A dermoscopic close-up of a skin lesion: 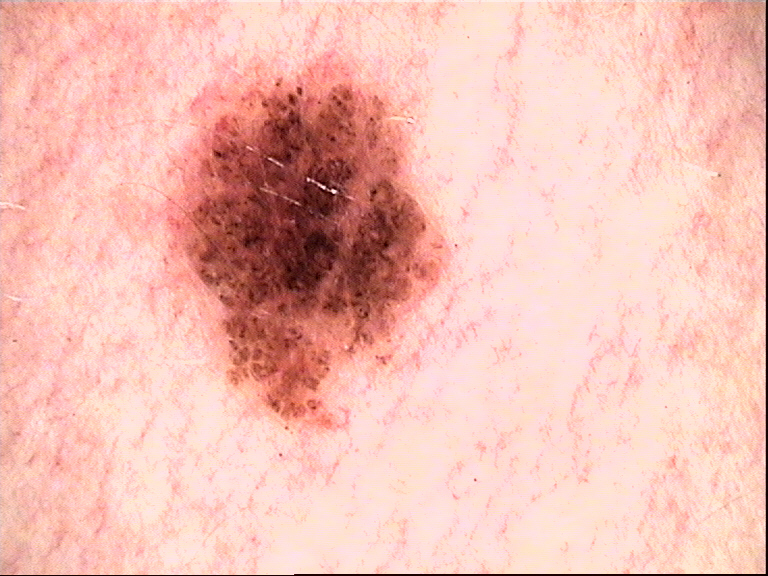Diagnosed as a dysplastic compound nevus.